Reported duration is three to twelve months. The patient is male. The patient described the issue as a rash. A close-up photograph. The lesion is associated with itching and bothersome appearance. The affected area is the leg. The lesion is described as raised or bumpy: 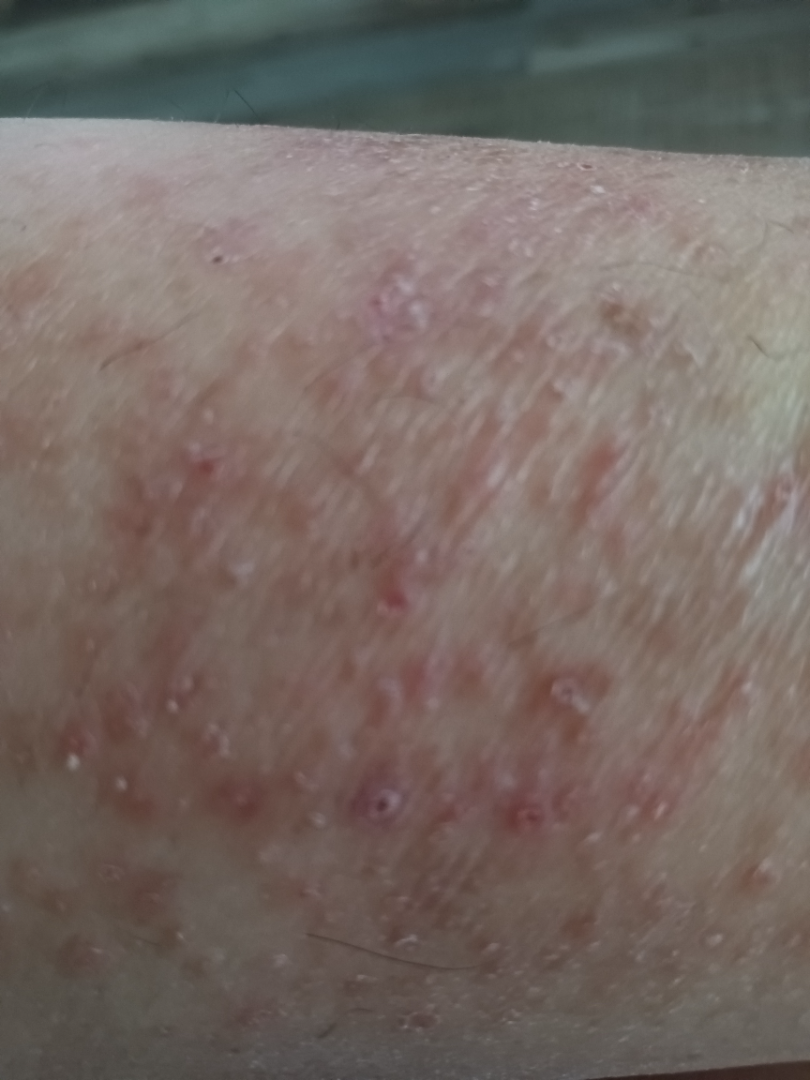<report>
<differential>
  <leading>Eczema</leading>
  <considered>Acute and chronic dermatitis</considered>
  <unlikely>Allergic Contact Dermatitis, Pigmented purpuric eruption, Drug Rash</unlikely>
</differential>
</report>